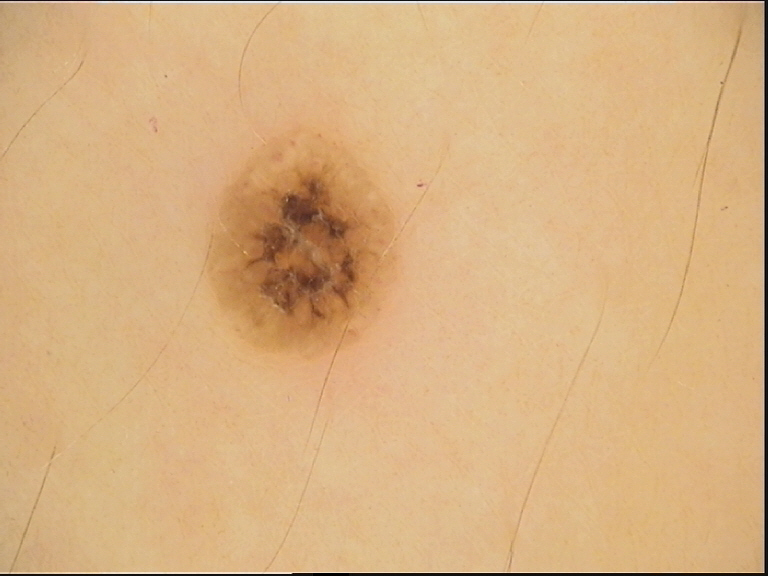{
  "image": "dermoscopy",
  "lesion_type": {
    "main_class": "keratinocytic"
  },
  "diagnosis": {
    "name": "seborrheic keratosis",
    "code": "sk",
    "malignancy": "benign",
    "super_class": "non-melanocytic",
    "confirmation": "expert consensus"
  }
}